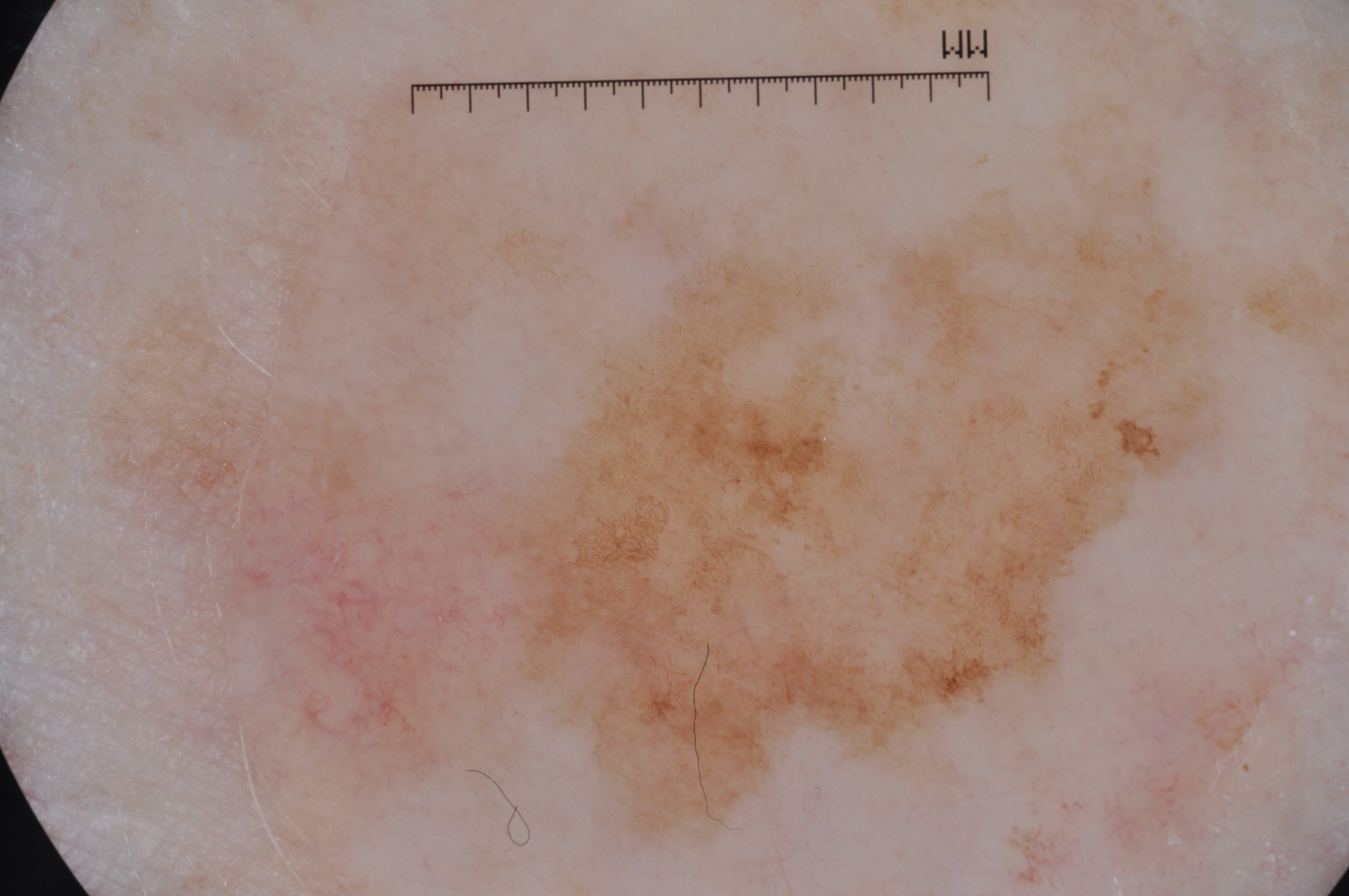Image and clinical context: A dermatoscopic image of a skin lesion. A female subject aged around 55. Dermoscopic review identifies pigment network and milia-like cysts. With coordinates (x1, y1, x2, y2), the lesion is located at bbox=[116, 203, 1233, 840]. Conclusion: Histopathology confirmed a melanoma.